A dermoscopic close-up of a skin lesion.
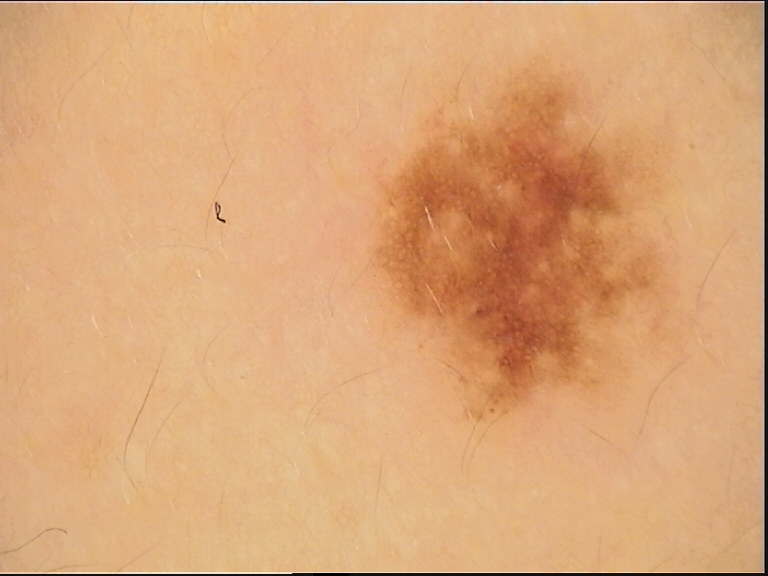label = dysplastic junctional nevus (expert consensus).